A dermatoscopic image of a skin lesion · a male patient in their 20s: 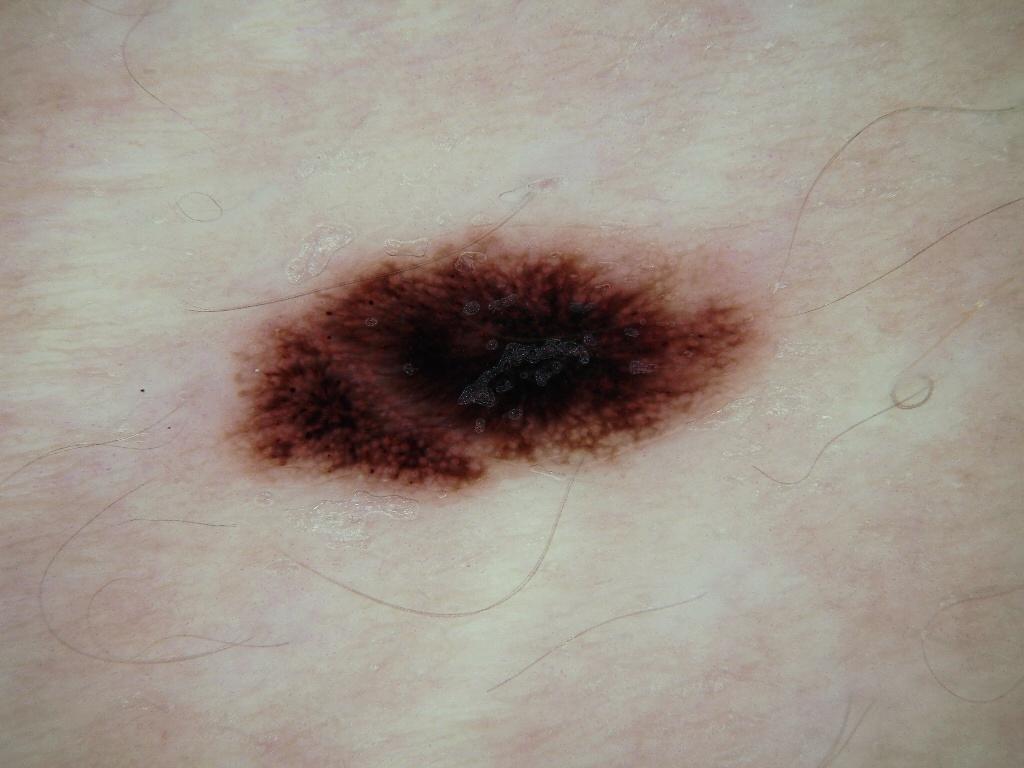<dermoscopy>
<lesion_extent>moderate</lesion_extent>
<dermoscopic_features>
  <present>pigment network, globules</present>
  <absent>milia-like cysts, negative network, streaks</absent>
</dermoscopic_features>
<lesion_location>
  <bbox_xyxy>213, 225, 768, 500</bbox_xyxy>
</lesion_location>
<diagnosis>
  <name>melanocytic nevus</name>
  <malignancy>benign</malignancy>
  <lineage>melanocytic</lineage>
  <provenance>clinical</provenance>
</diagnosis>
</dermoscopy>